The patient says their skin reddens with sun exposure · a female subject age 59 · the patient describes having a moderate number of moles · a clinical photograph showing a skin lesion · by self-report, no immunosuppression.
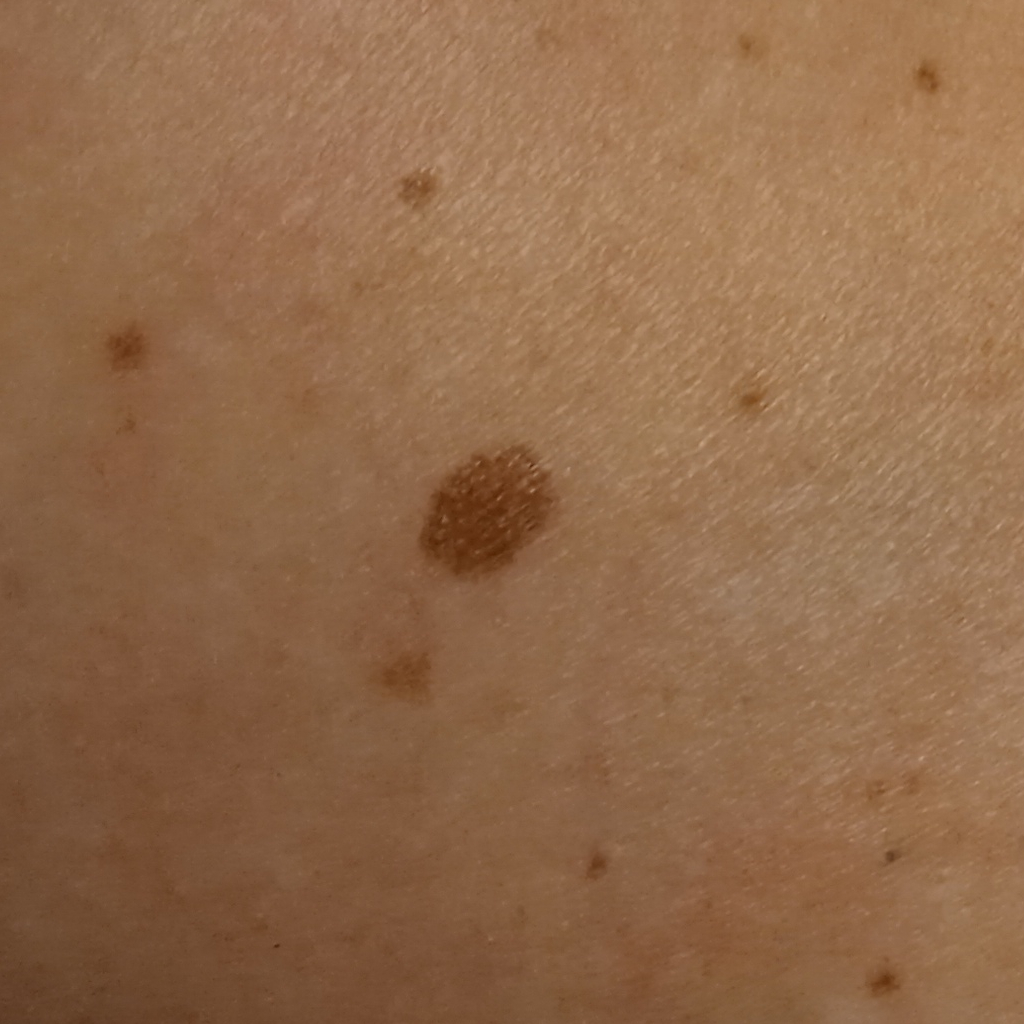body site: an arm | diagnosis: atypical (dysplastic) nevus — biopsy-proven.